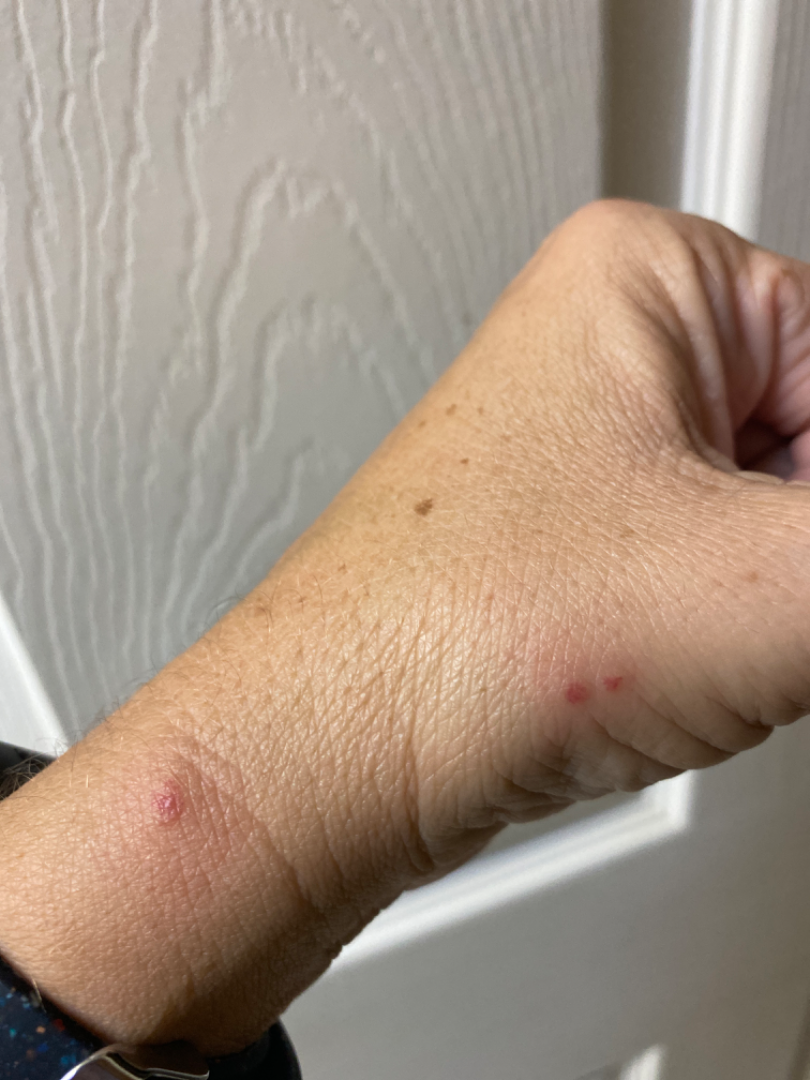| feature | finding |
|---|---|
| present for | one to four weeks |
| constitutional symptoms | none reported |
| shot type | at an angle |
| body site | back of the hand |
| reported symptoms | pain |
| texture | raised or bumpy |
| patient describes the issue as | a rash |
| differential diagnosis | favoring Insect Bite |